The patient notes the condition has been present for about one day, the photo was captured at an angle, the patient reported no systemic symptoms, the lesion involves the arm, skin tone: Fitzpatrick skin type II; human graders estimated Monk Skin Tone 2 or 3 (two reviewer pools), the lesion is associated with itching, the patient notes the lesion is flat and raised or bumpy:
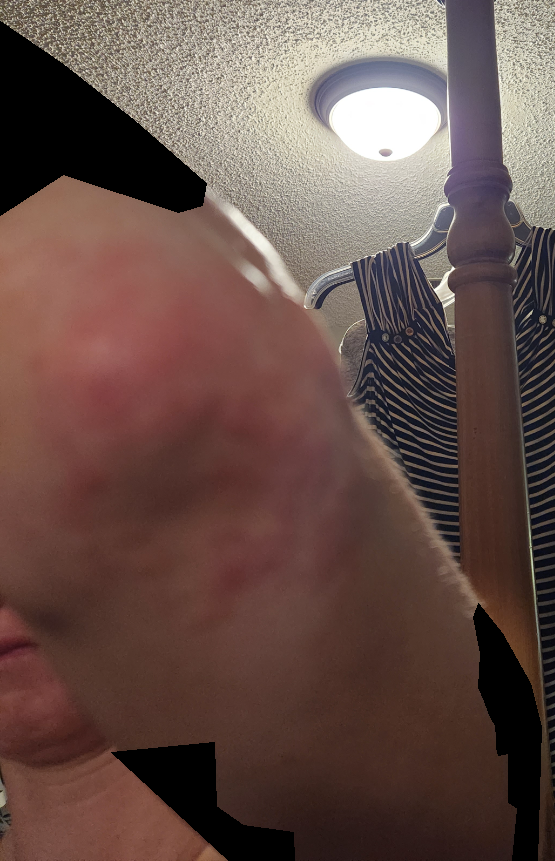| key | value |
|---|---|
| assessment | unable to determine |